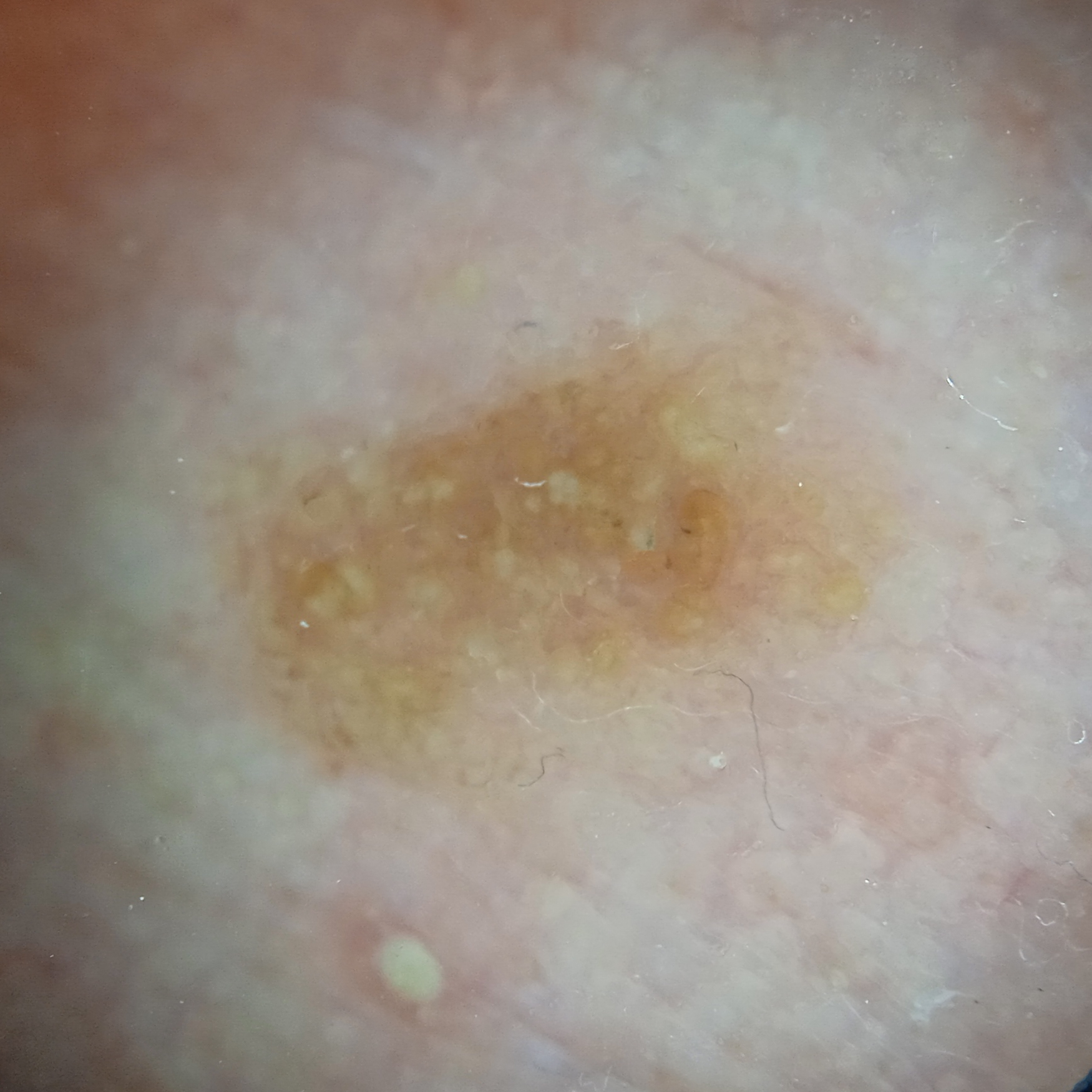Case:
– risk factors: no prior organ transplant, no personal history of cancer
– subject: male, age 89
– image type: dermoscopy
– sun reaction: skin reddens painfully with sun exposure
– referral context: research study (no referral diagnosis)
– location: the face
– diameter: 6.4 mm
– assessment: actinic keratosis (dermatologist consensus)